The patient notes the condition has been present for one to four weeks · the patient also reports fever · texture is reported as fluid-filled and raised or bumpy · skin tone: self-reported Fitzpatrick skin type III · the contributor is a female aged 18–29 · the leg is involved · the photo was captured at a distance · symptoms reported: itching, bothersome appearance and pain · the patient considered this a rash: 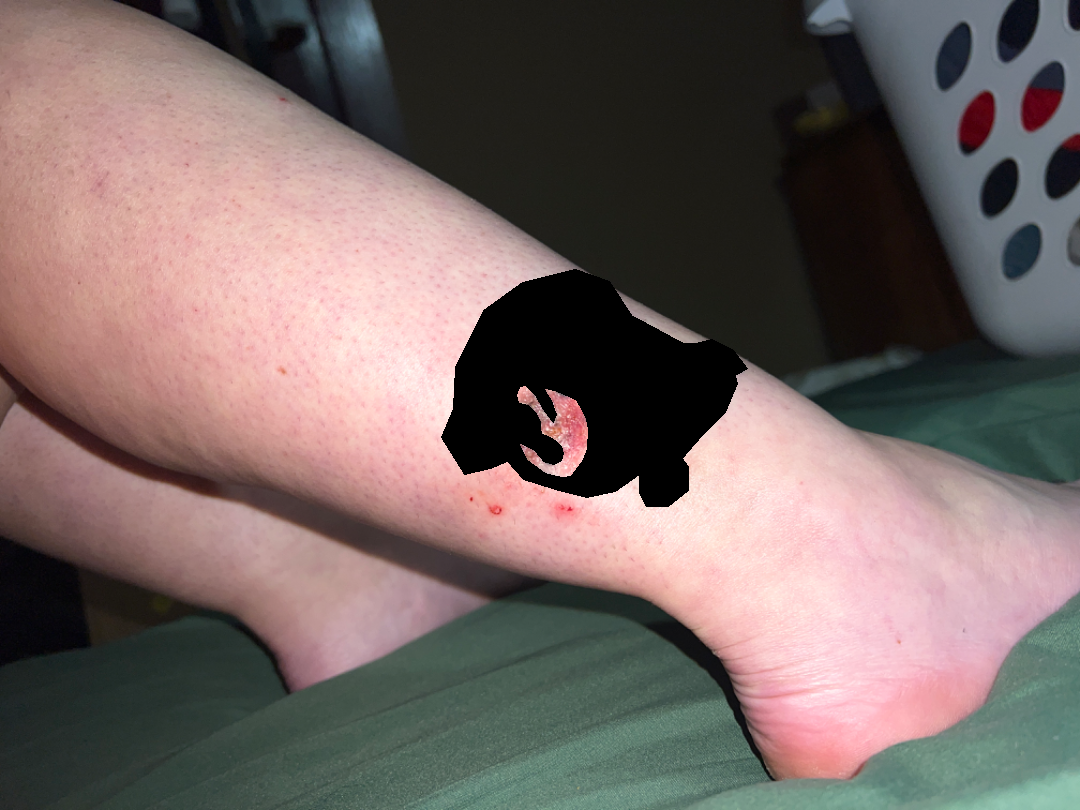Diagnostic features were not clearly distinguishable in this photograph.